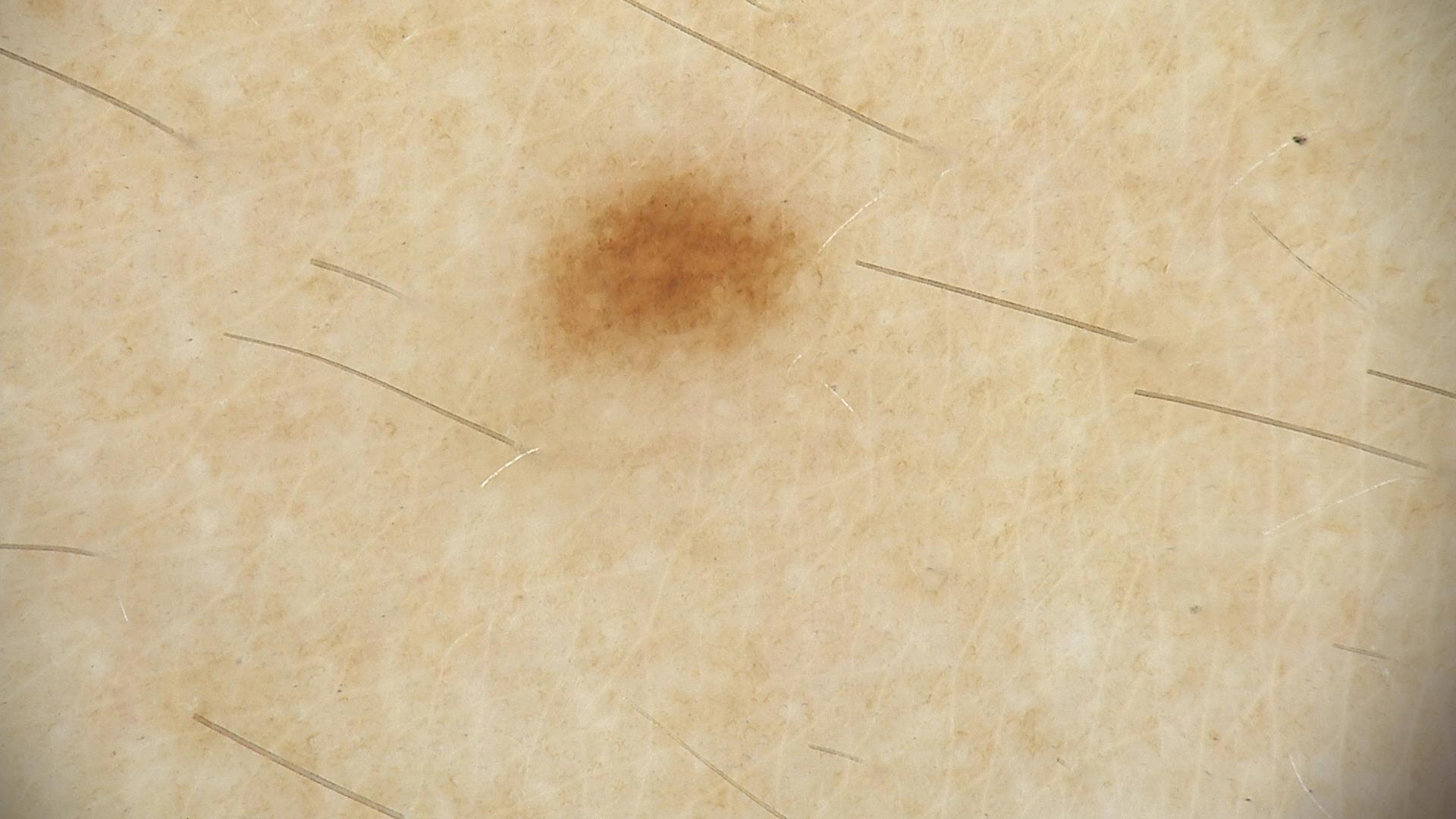Diagnosed as a dysplastic junctional nevus.